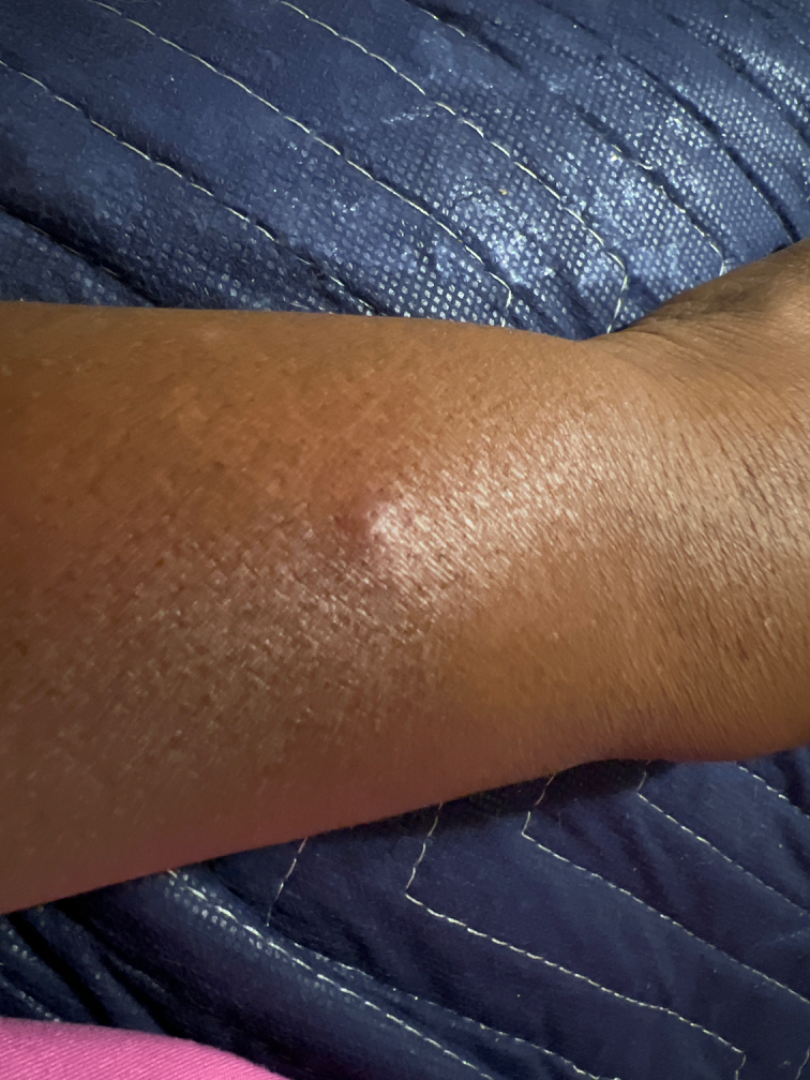Patient information:
Close-up view.
Review:
The primary impression is Cyst; also raised was Lipoma.